A dermoscopy image of a single skin lesion: 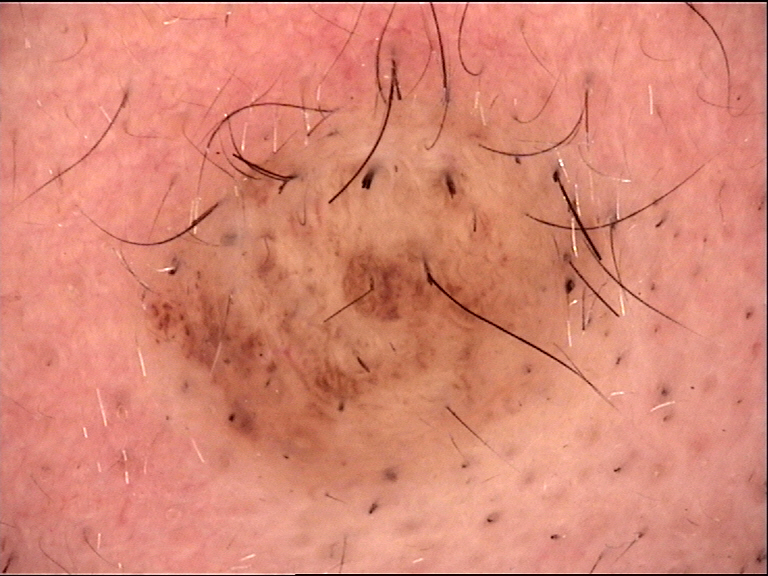* category: banal
* class: dermal nevus (expert consensus)